A dermoscopic close-up of a skin lesion.
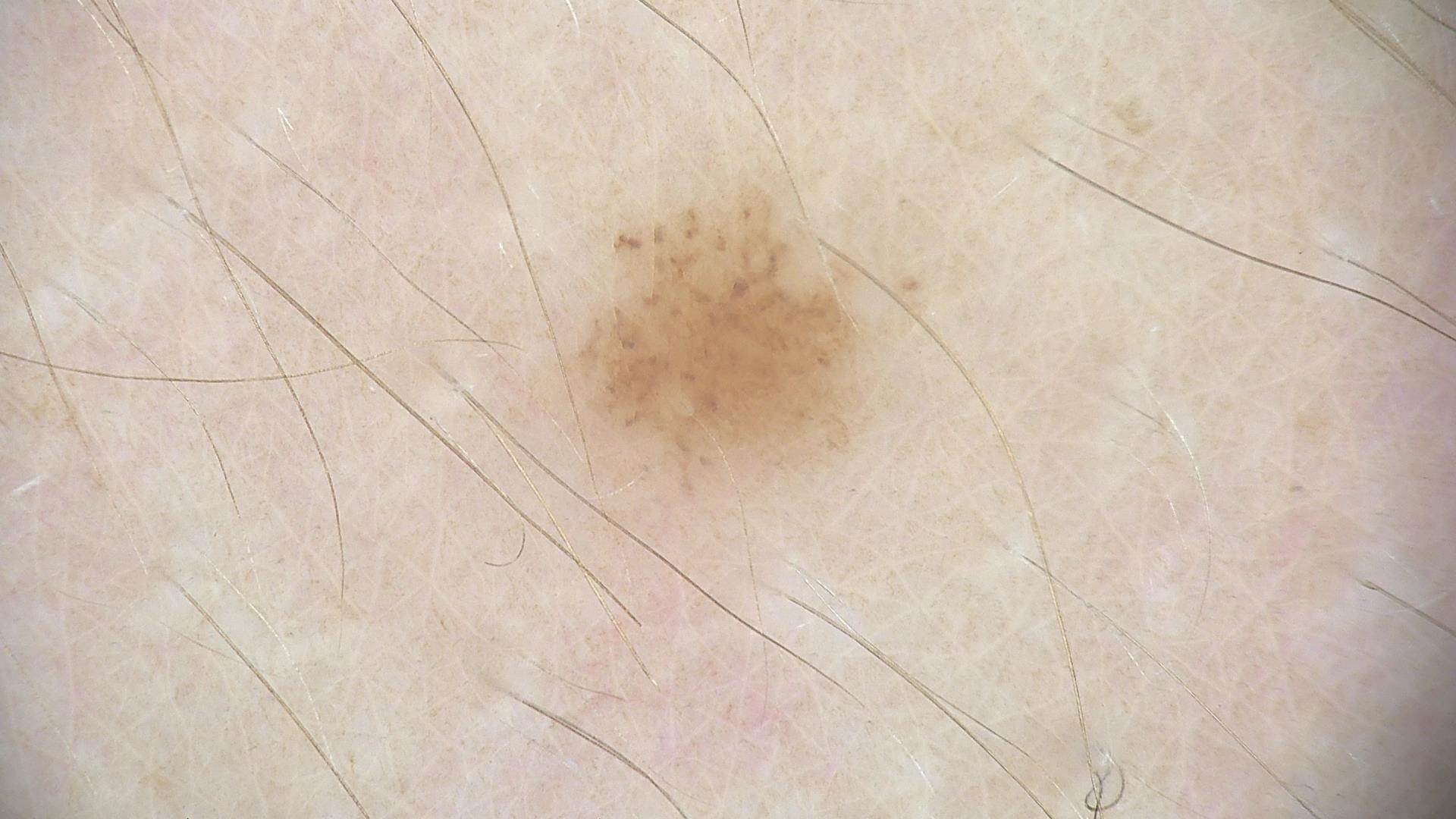diagnostic label: dysplastic junctional nevus (expert consensus)